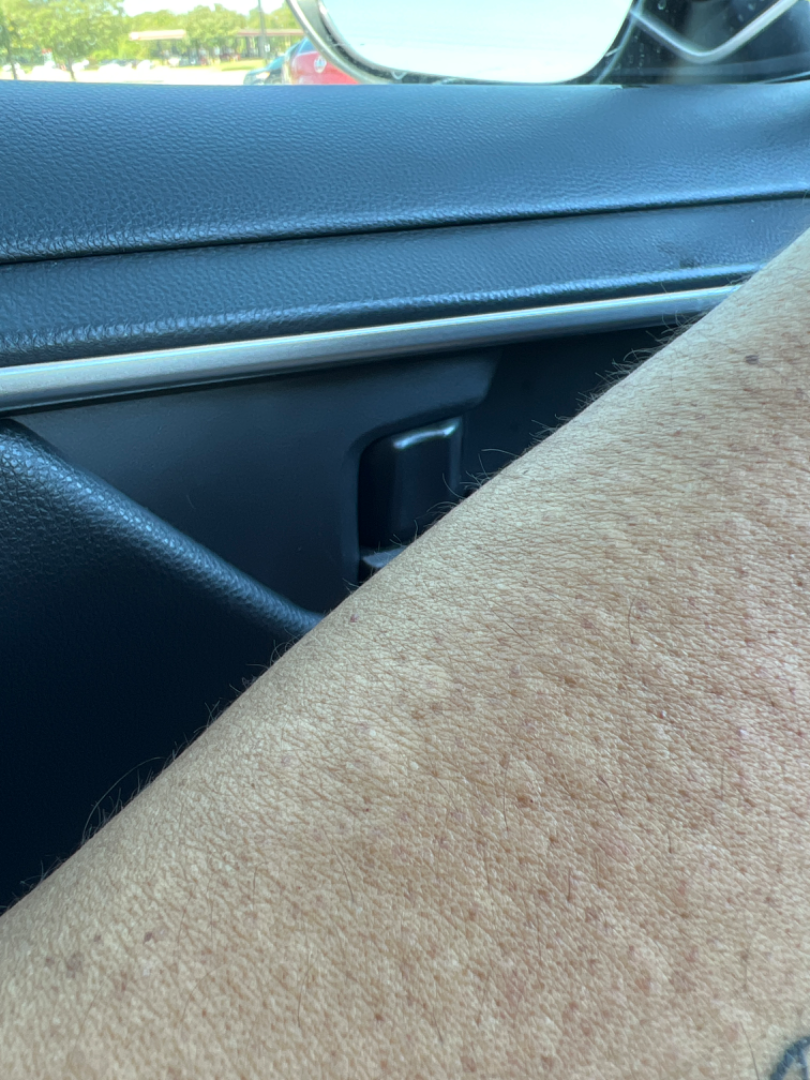assessment = unable to determine | framing = at an angle | site = arm and leg.